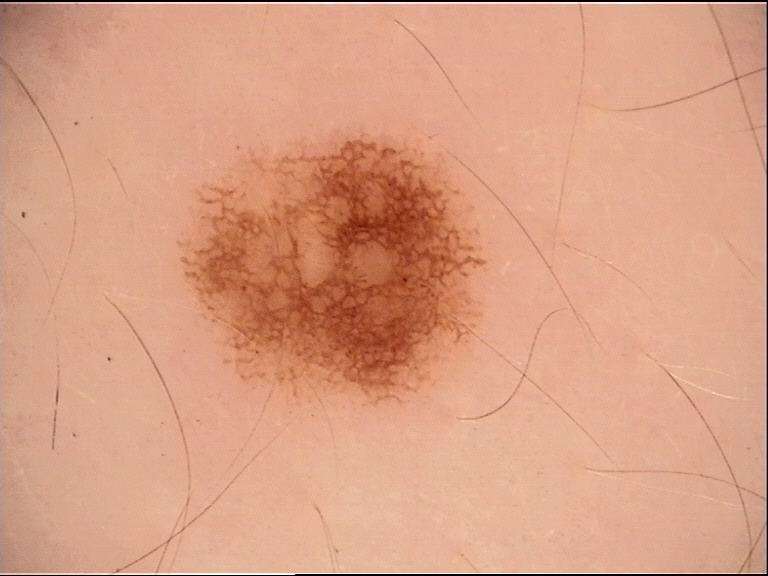assessment = dysplastic junctional nevus (expert consensus).